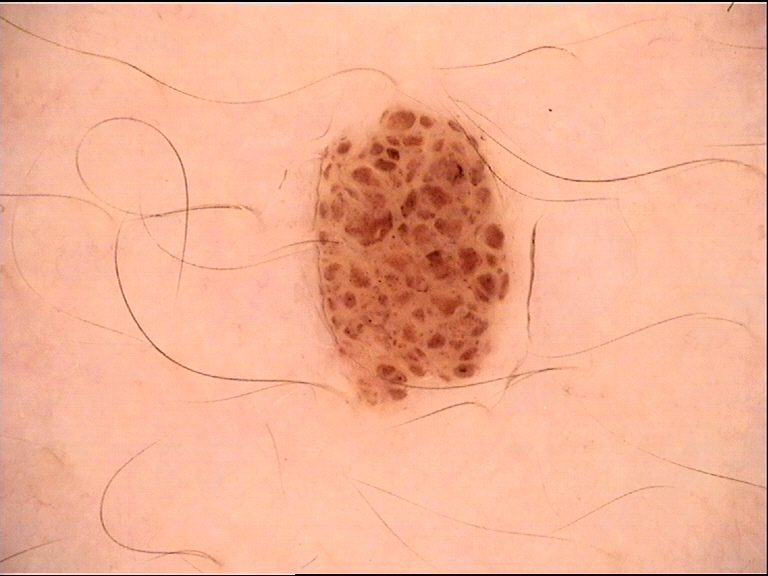A dermatoscopic image of a skin lesion. The architecture is that of a banal lesion. Diagnosed as a compound nevus.